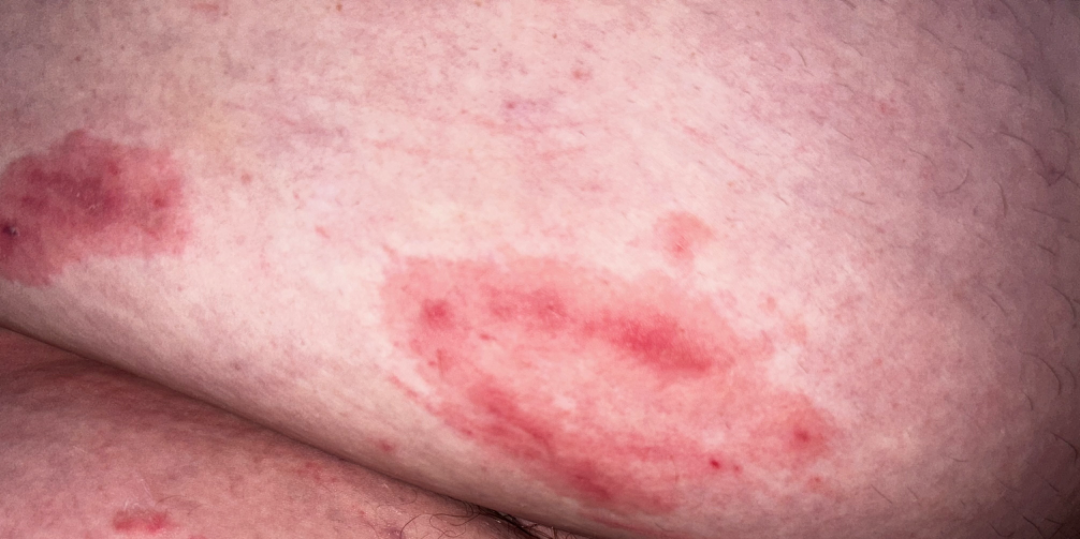Q: Could the case be diagnosed?
A: not assessable
Q: What is the affected area?
A: front of the torso
Q: Image view?
A: close-up